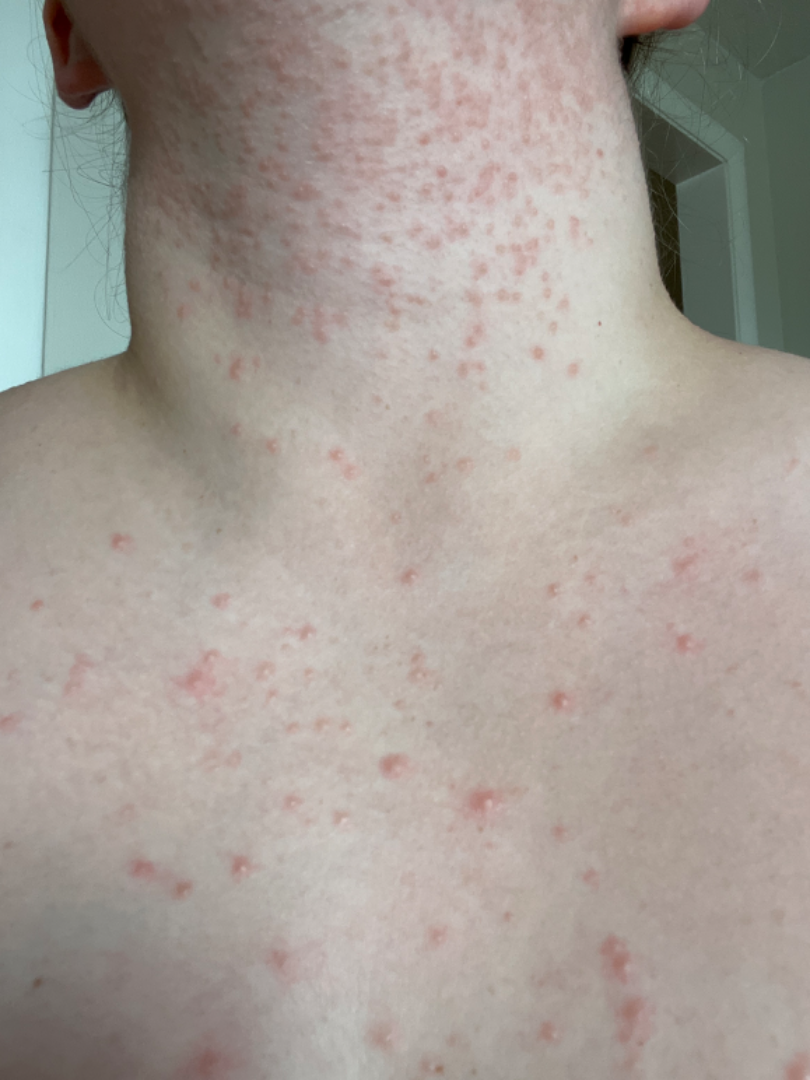| key | value |
|---|---|
| patient | female, age 18–29 |
| shot type | close-up |
| body site | arm, front of the torso, back of the hand and head or neck |
| dermatologist impression | Acne (most likely); Folliculitis (possible) |